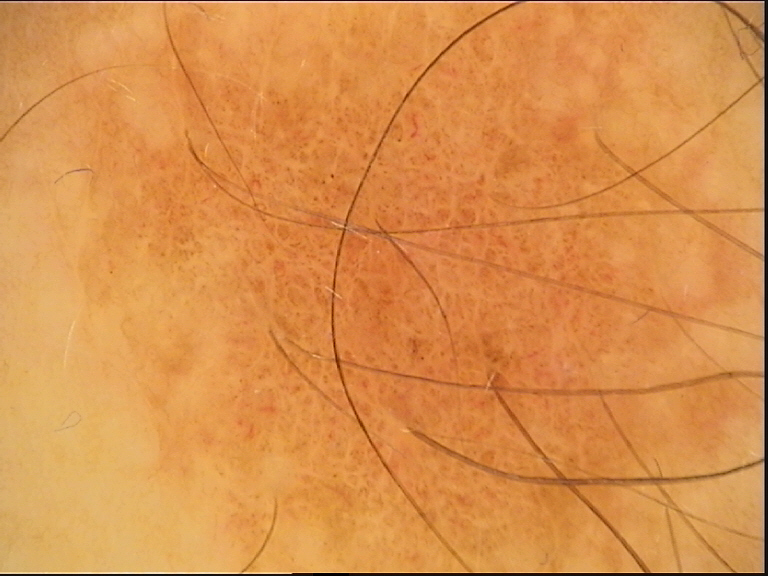modality: dermatoscopy | diagnosis: dysplastic junctional nevus (expert consensus).